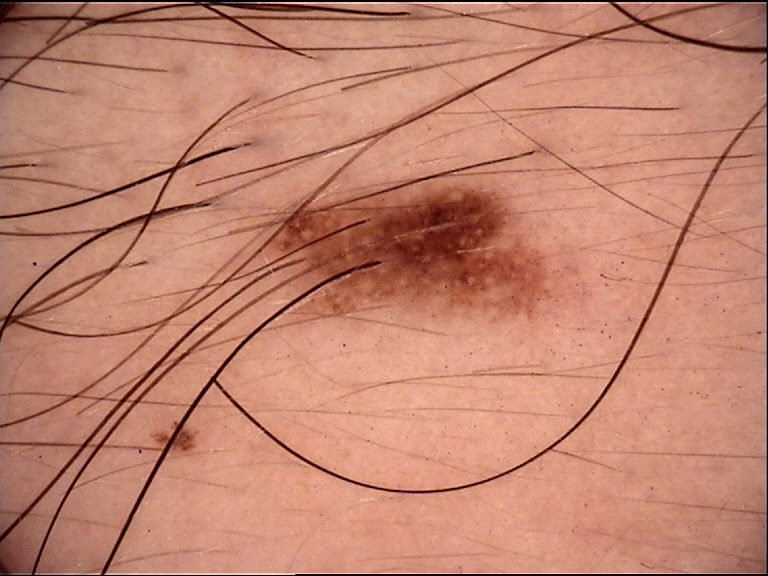A dermoscopic photograph of a skin lesion. The diagnosis was a dysplastic junctional nevus.